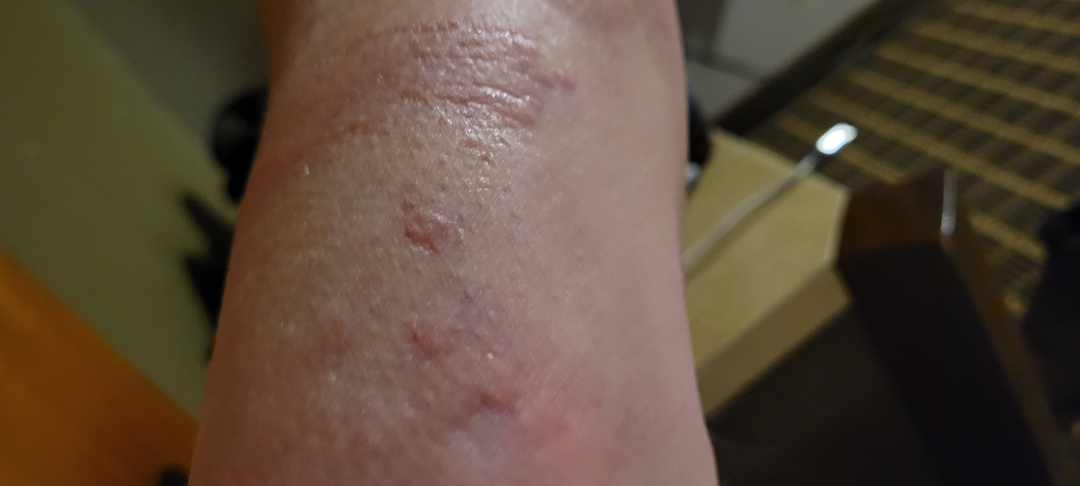Notes:
• assessment: not assessable
• photo taken: close-up